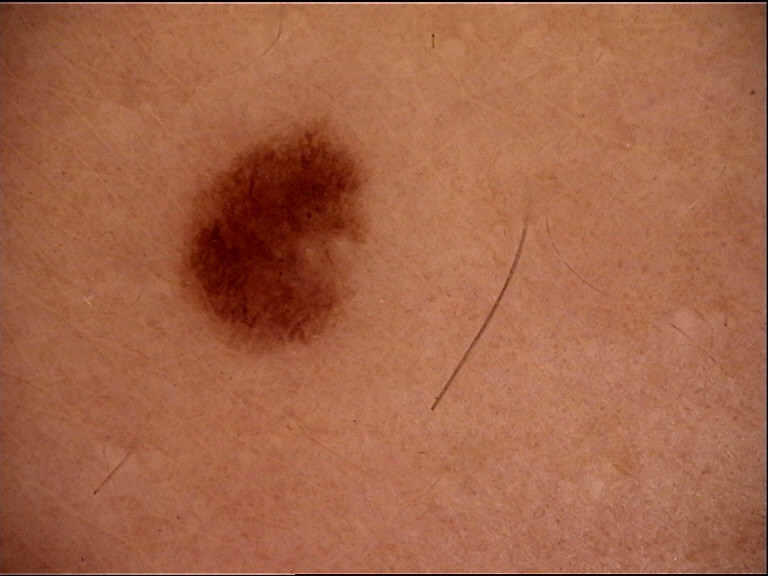Dermoscopy of a skin lesion.
Labeled as a benign lesion — a dysplastic junctional nevus.